Female contributor, age 40–49. Close-up view:
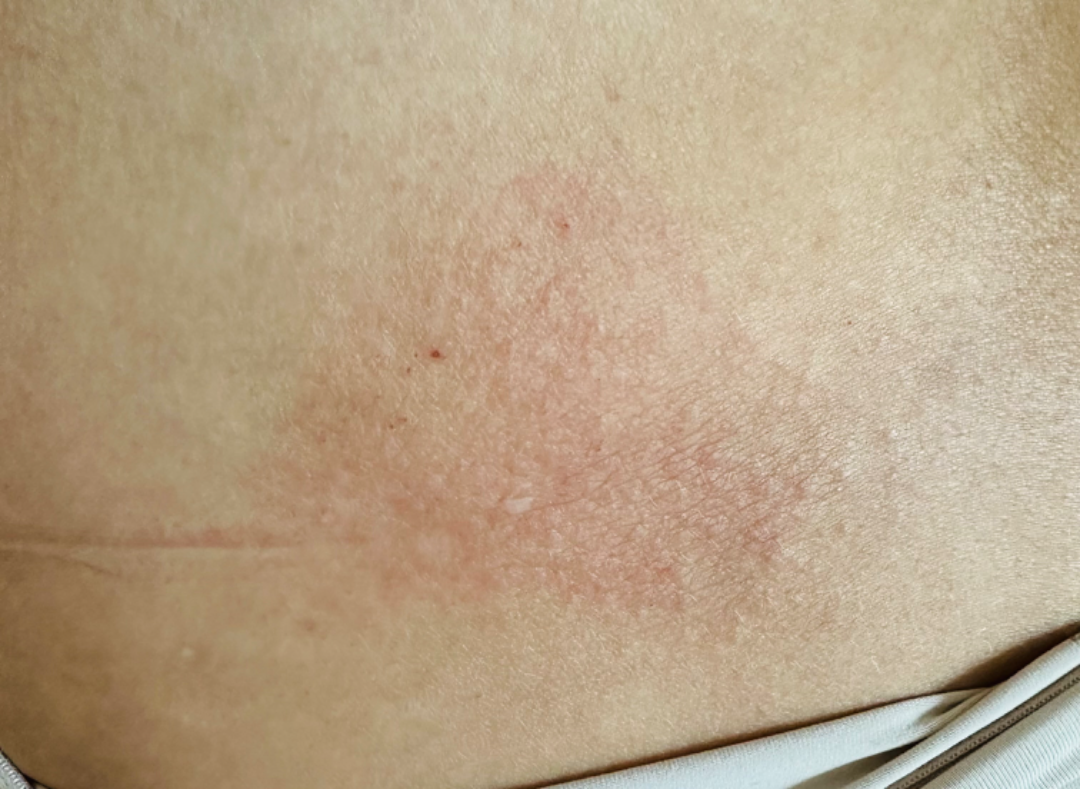Impression:
The reviewing clinician's impression was: Amyloidosis of skin (67%); Lichen Simplex Chronicus (33%).